A dermatoscopic image of a skin lesion · a female patient, aged 58-62: 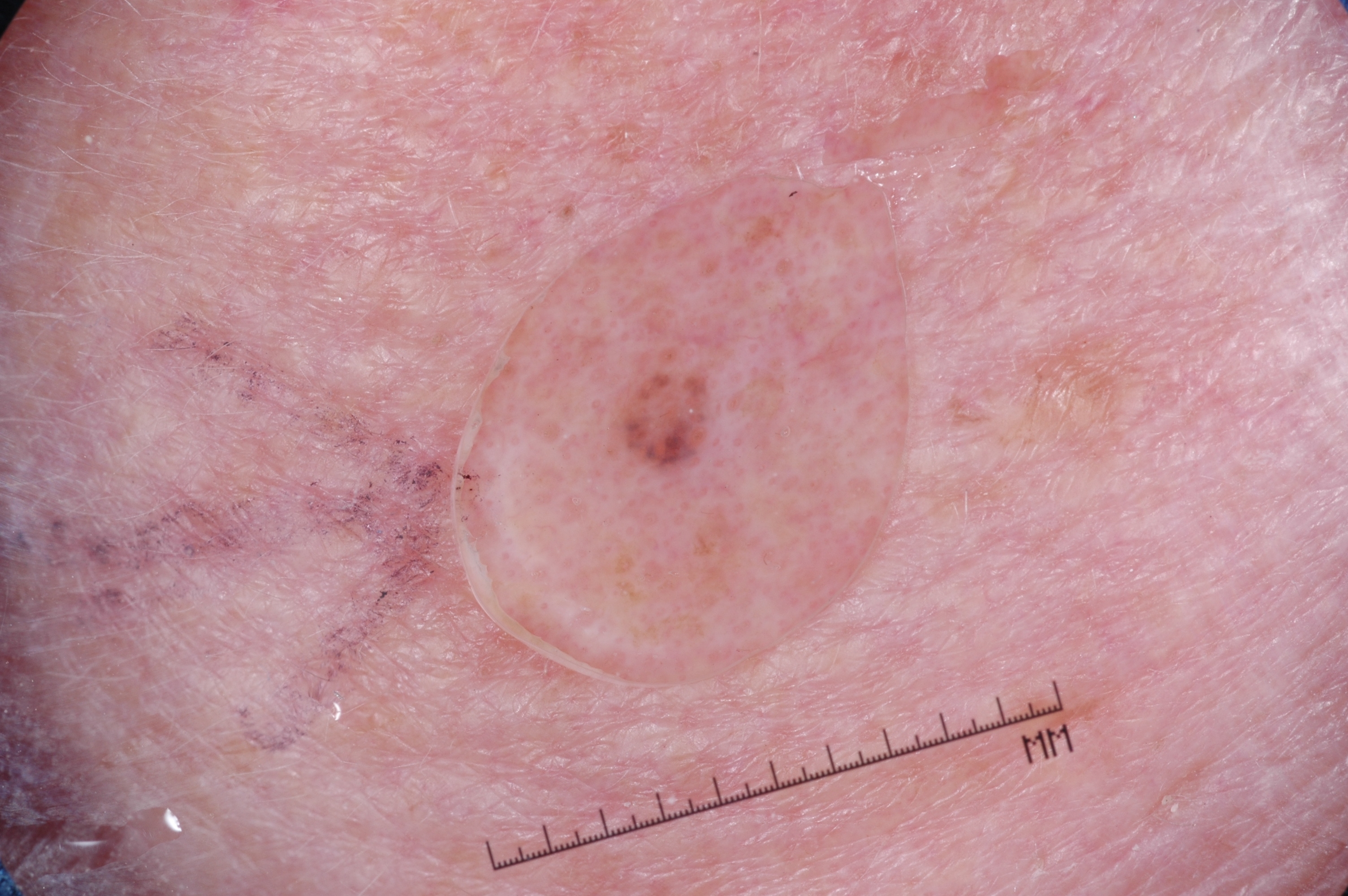With coordinates (x1, y1, x2, y2), the lesion is located at <box>613, 370, 707, 474</box>. Dermoscopic assessment notes milia-like cysts, with no pigment network, negative network, or streaks. The lesion occupies roughly 1% of the field. Expert review diagnosed this as a melanocytic nevus, a benign lesion.